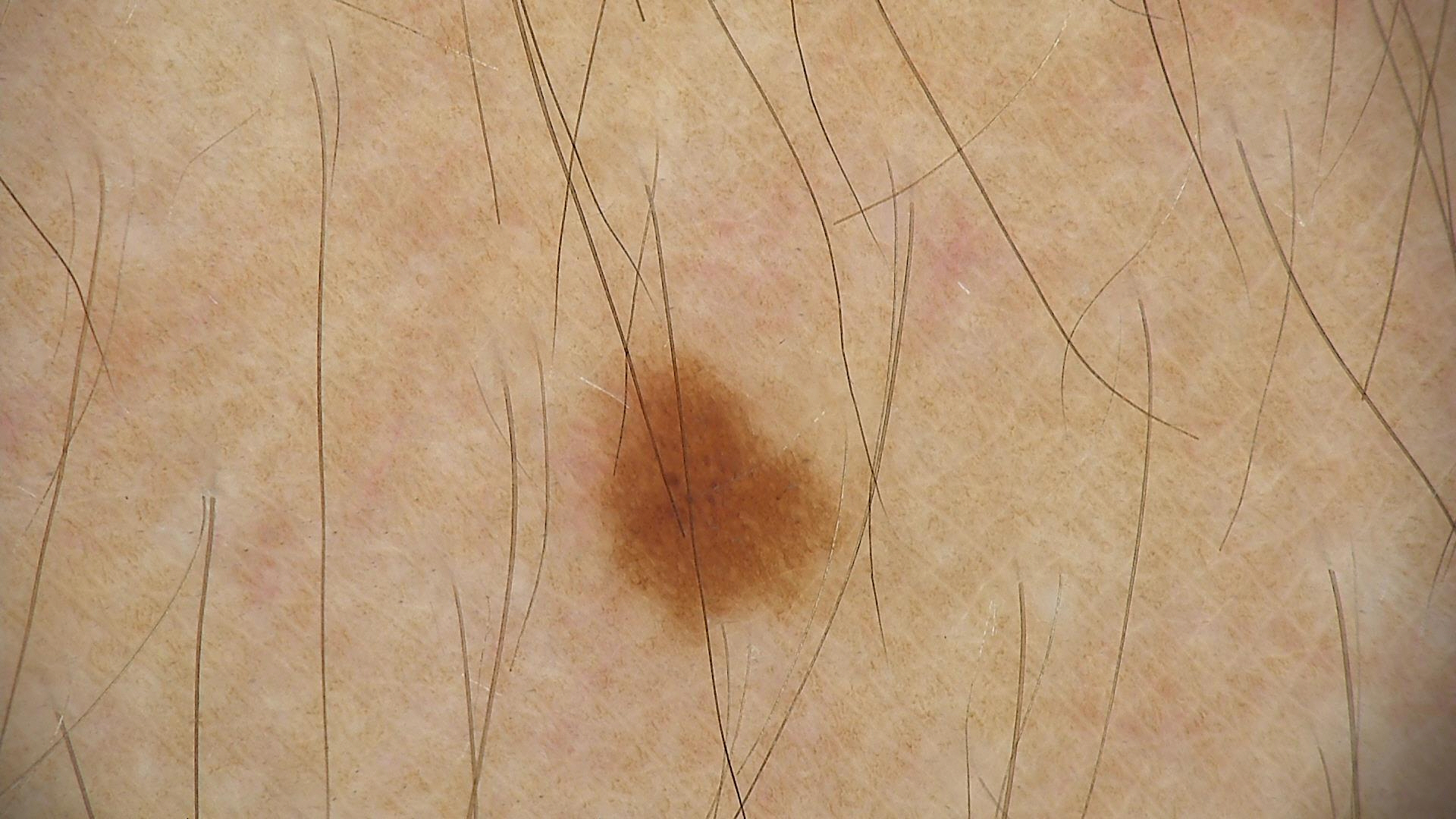  diagnosis:
    name: dysplastic junctional nevus
    code: jd
    malignancy: benign
    super_class: melanocytic
    confirmation: expert consensus